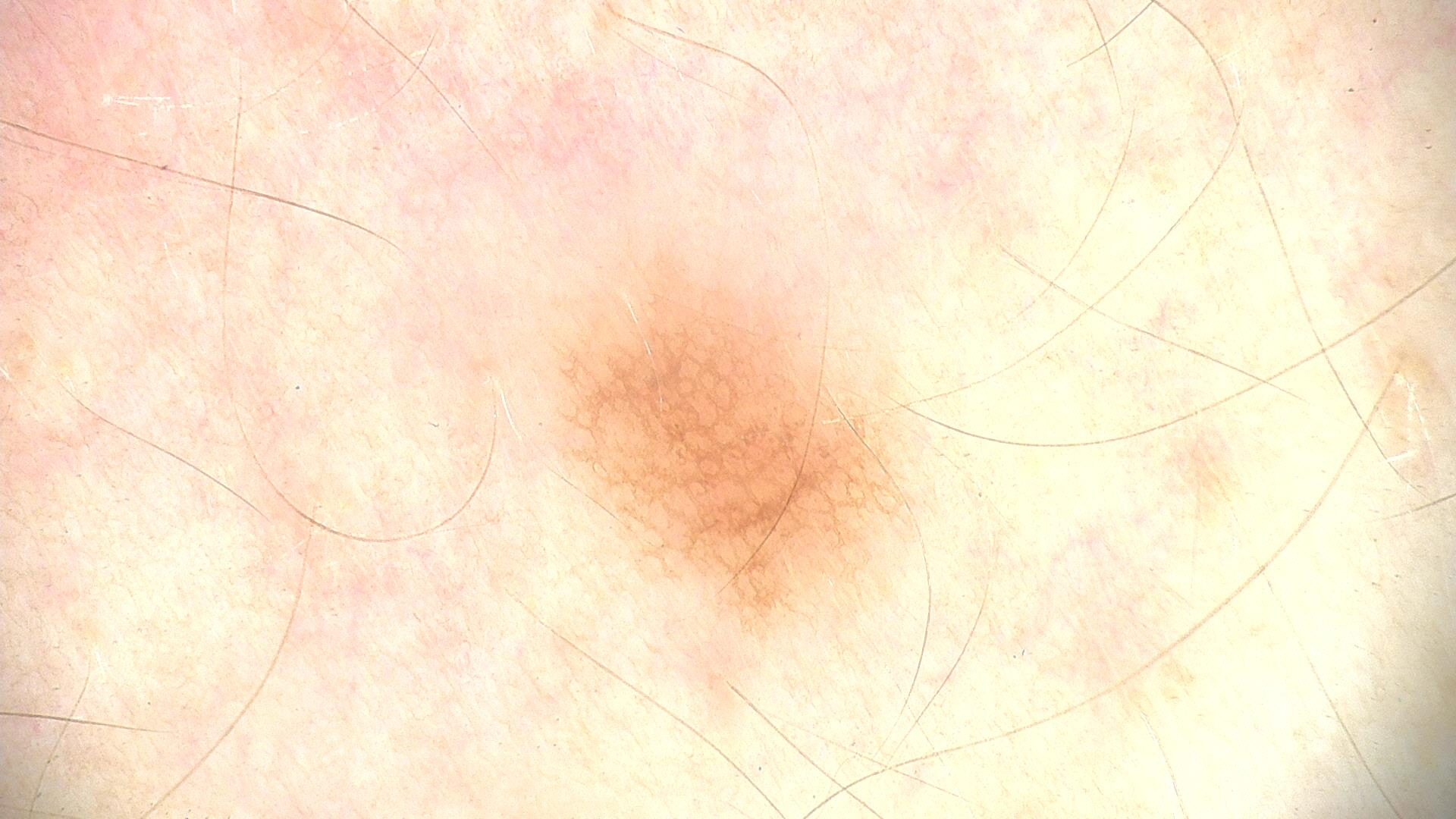Summary:
A dermatoscopic image of a skin lesion.
Impression:
Diagnosed as a benign lesion — a dysplastic junctional nevus.